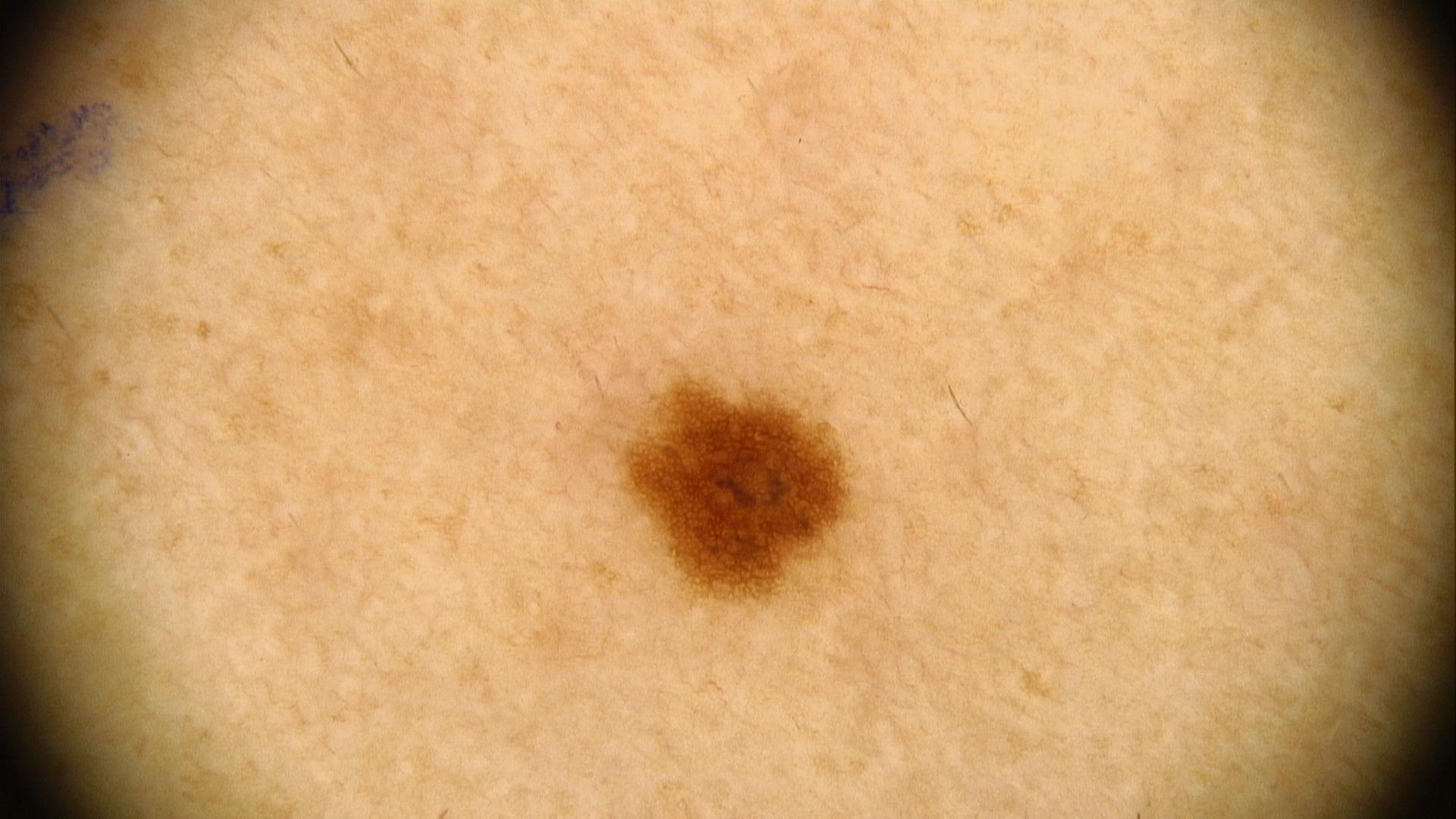{
  "skin_type": "III",
  "image": "contact-polarized dermoscopy",
  "diagnosis": {
    "name": "Nevus",
    "malignancy": "benign",
    "confirmation": "expert clinical impression",
    "lineage": "melanocytic"
  }
}